This is a close-up image: 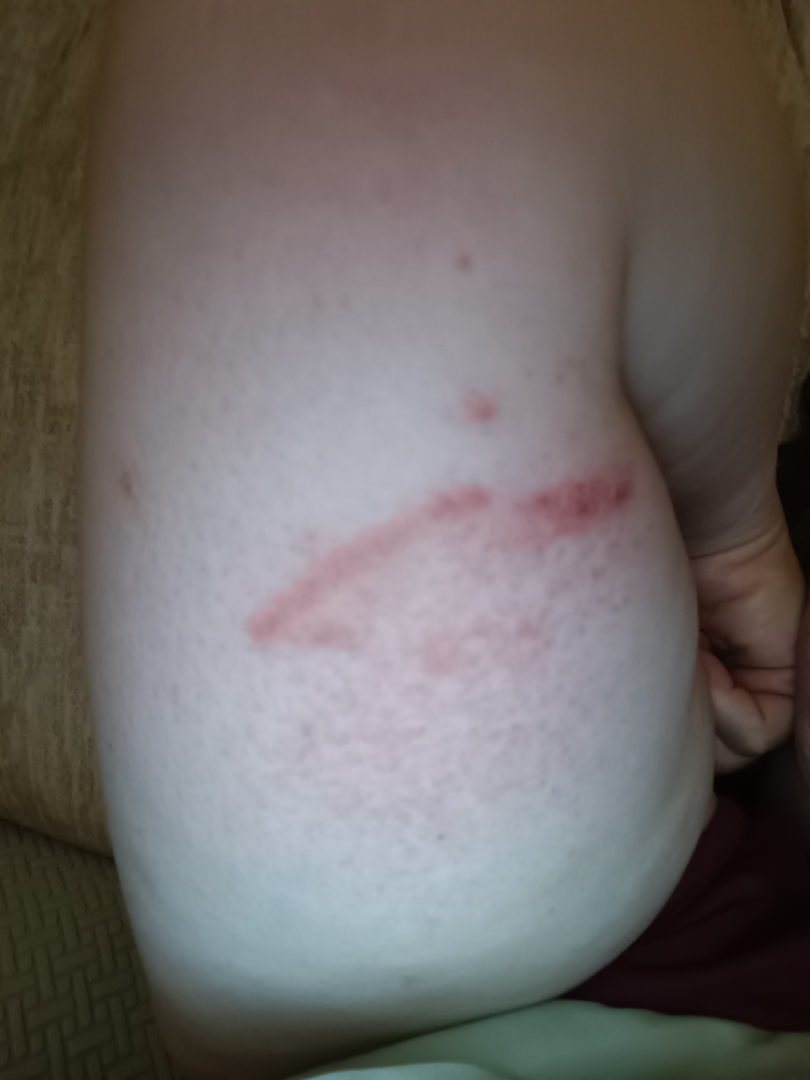| field | value |
|---|---|
| assessment | indeterminate from the photograph |